Female contributor, age 18–29; this is a close-up image; located on the arm:
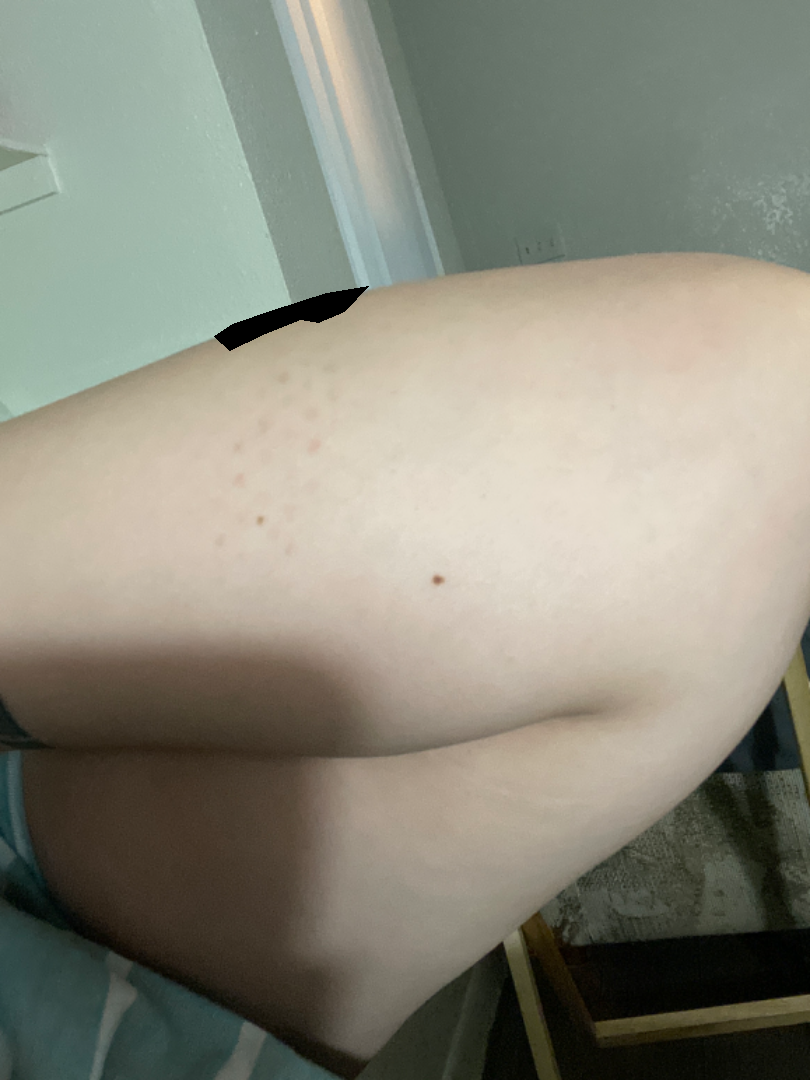Q: What was the assessment?
A: indeterminate